A dermoscopy image of a single skin lesion.
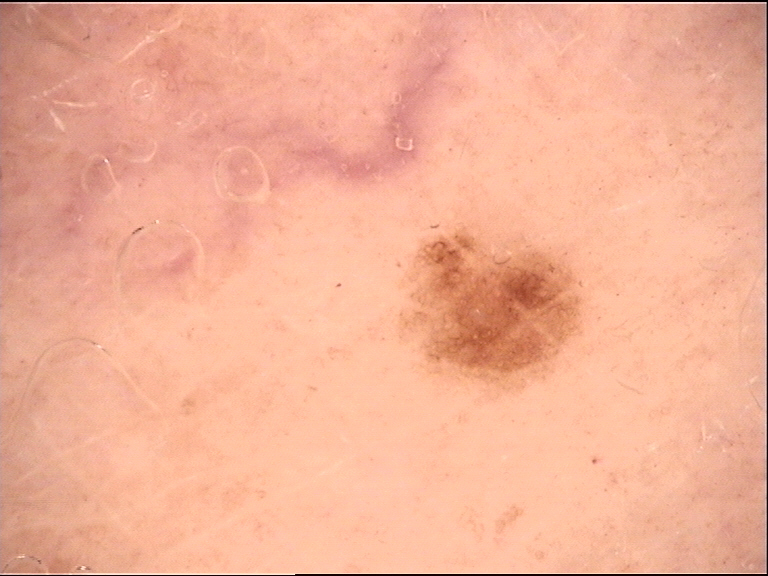<case>
<diagnosis>
<name>dysplastic junctional nevus</name>
<code>jd</code>
<malignancy>benign</malignancy>
<super_class>melanocytic</super_class>
<confirmation>expert consensus</confirmation>
</diagnosis>
</case>